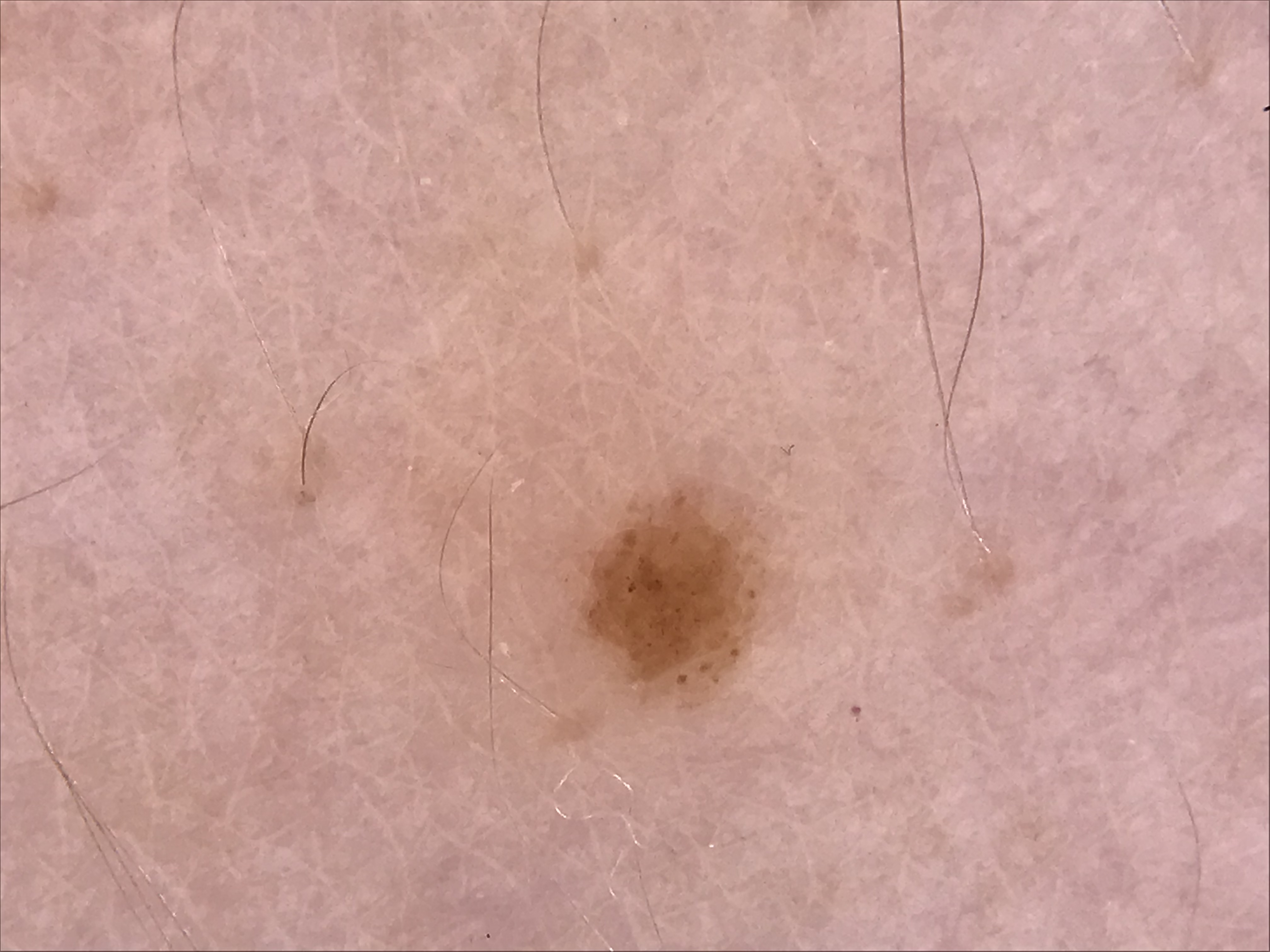Impression:
Classified as a junctional nevus.